The patient reports a personal history of cancer, a family history of skin cancer, and a personal history of skin cancer · the patient says their skin reddens with sun exposure · a clinical photograph of a skin lesion — 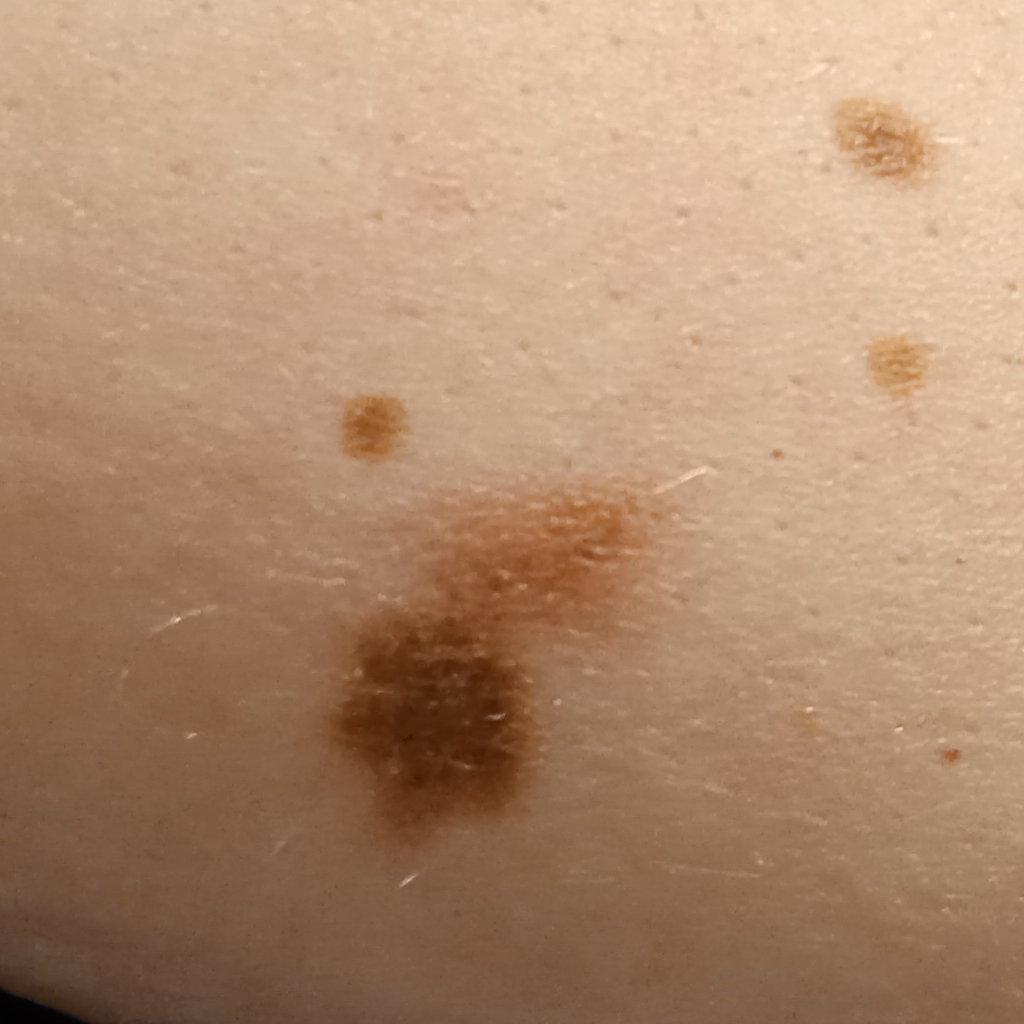<case>
  <lesion_size>
    <diameter_mm>17.5</diameter_mm>
  </lesion_size>
  <diagnosis>
    <name>melanoma</name>
    <malignancy>malignant</malignancy>
  </diagnosis>
</case>